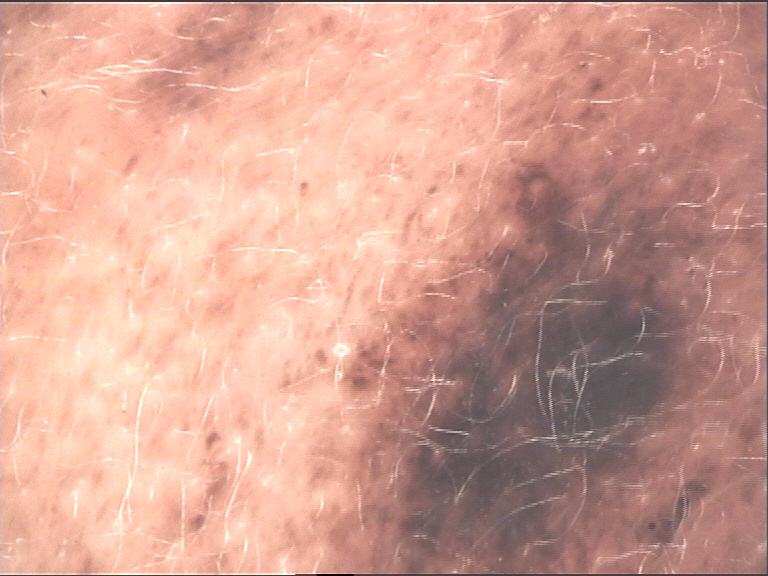Q: What is this lesion?
A: congenital compound nevus (expert consensus)